Present for about one day, skin tone: non-clinician graders estimated 3 on the MST, the lesion involves the arm, this image was taken at an angle, texture is reported as flat, the subject is a male aged 18–29: 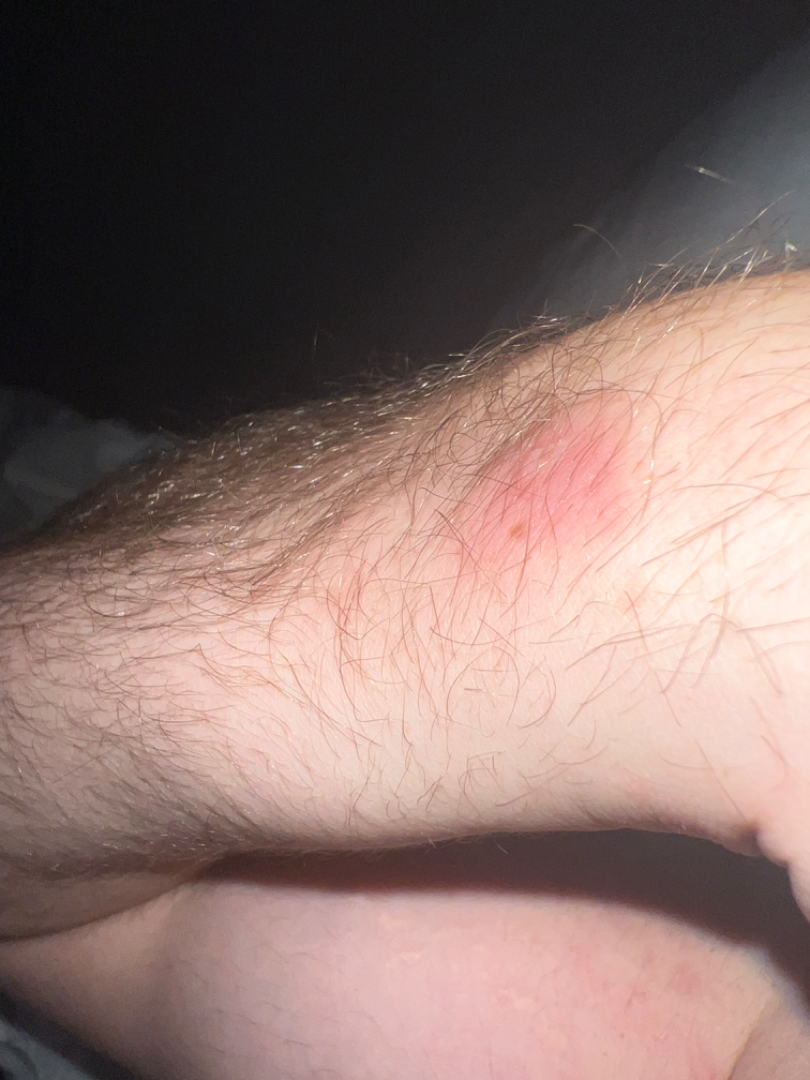{
  "assessment": "could not be assessed"
}